A dermatoscopic image of a skin lesion, a male patient aged approximately 30: 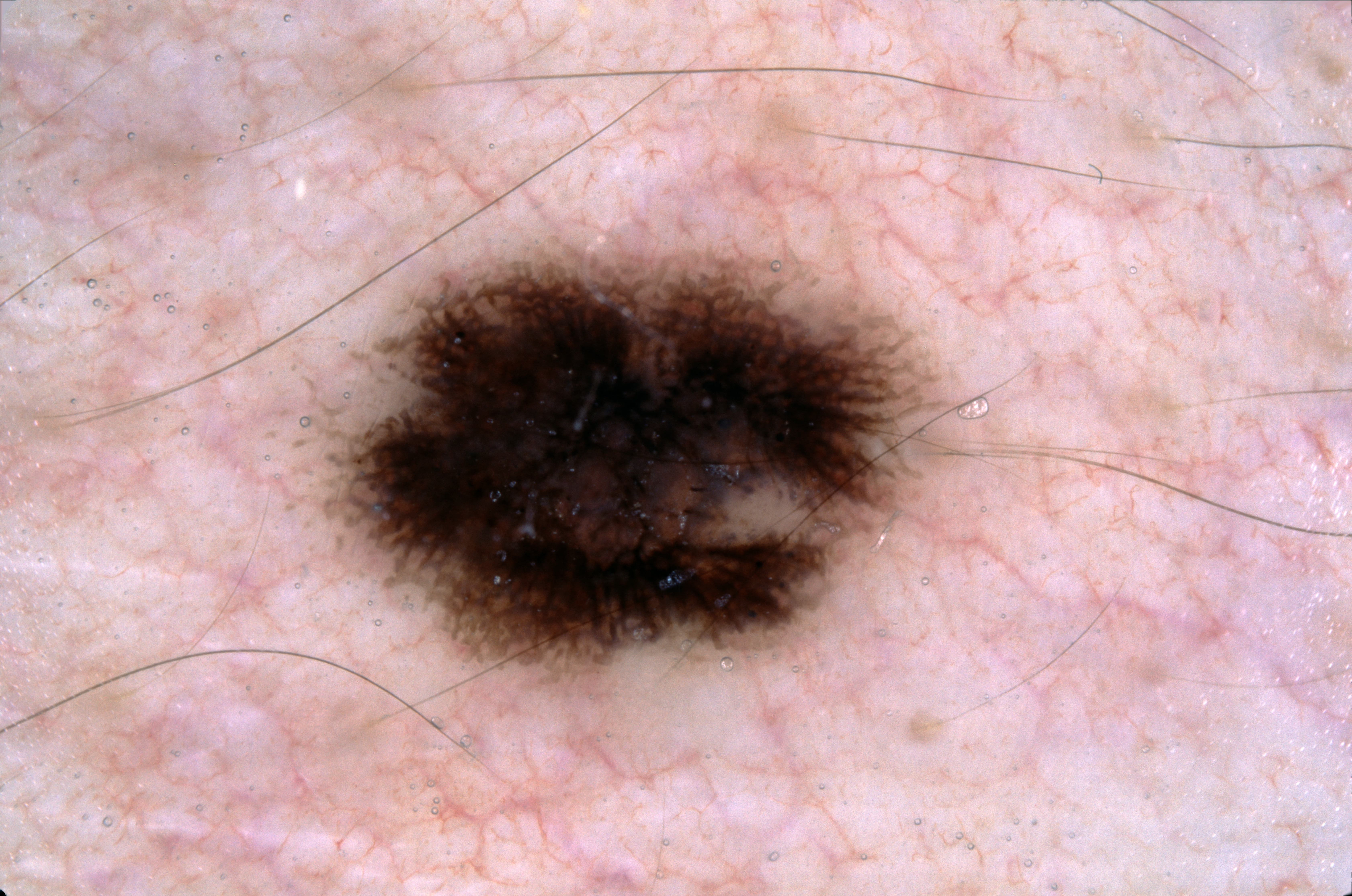Image and clinical context: Dermoscopy demonstrates pigment network, with no streaks, milia-like cysts, or negative network. As (left, top, right, bottom), the lesion is bounded by bbox(338, 252, 929, 679). The lesion takes up a moderate portion of the field. Impression: Expert review diagnosed this as a melanocytic nevus, a benign skin lesion.